Few moles overall by the patient's own estimate. A clinical close-up of a skin lesion. The patient says their skin reddens with sun exposure. A male subject 66 years old.
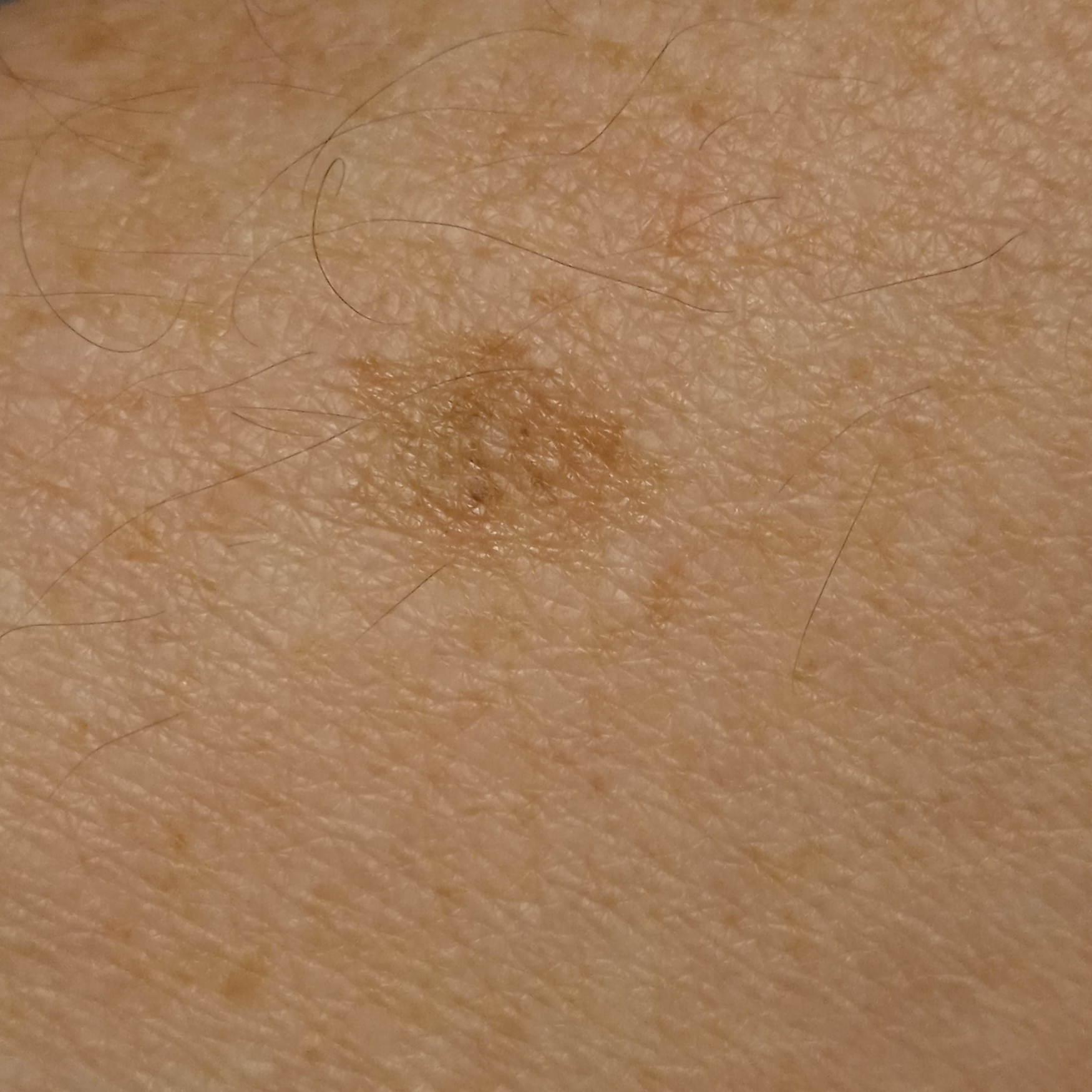  lesion_location: an arm
  lesion_size:
    diameter_mm: 12.4
  diagnosis:
    name: melanoma
    malignancy: malignant